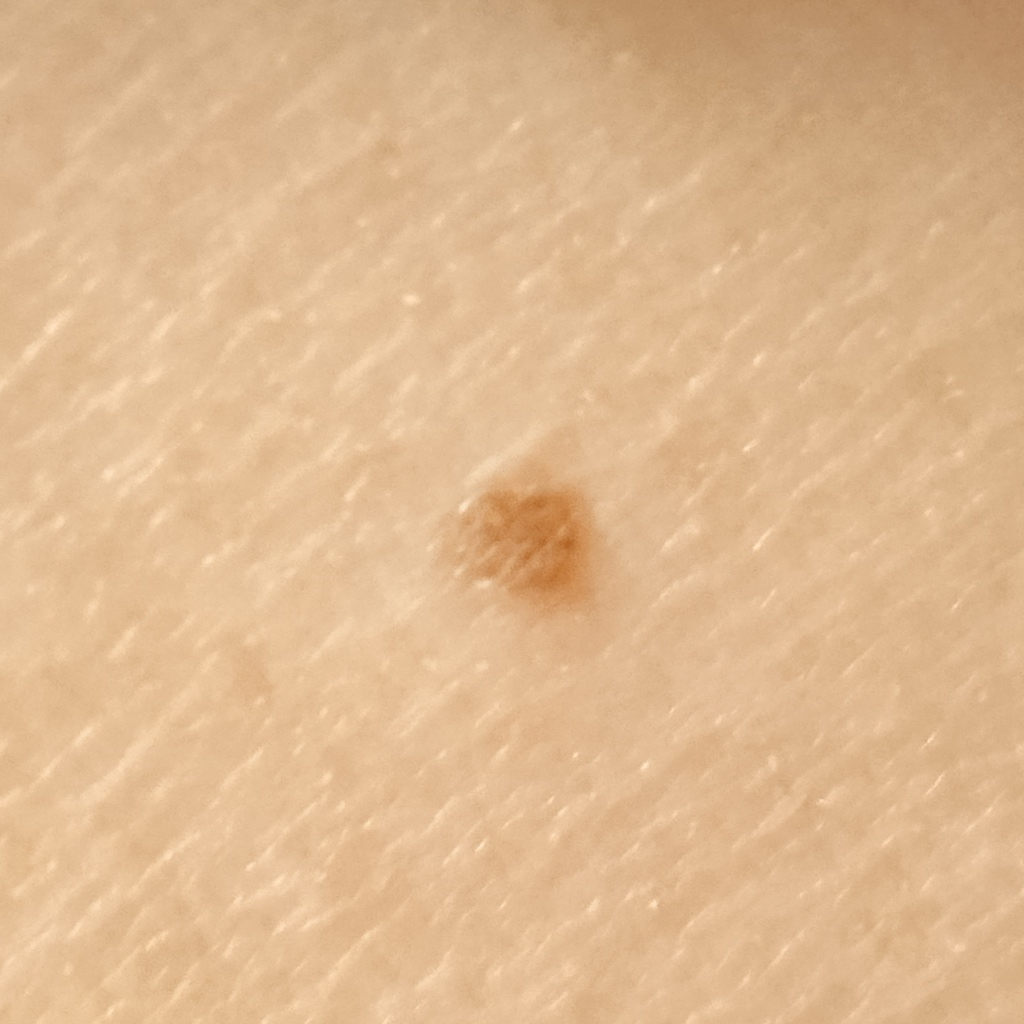Findings:
* nevus count: a moderate number of melanocytic nevi
* sun reaction: skin reddens painfully with sun exposure
* referral context: research study (no referral diagnosis)
* patient: female, 50 years old
* modality: clinical photograph
* body site: the back
* size: 2.2 mm
* diagnosis: melanocytic nevus (dermatologist consensus)